The photograph is a close-up of the affected area. Female contributor, age 50–59. Reported lesion symptoms include itching. Reported duration is less than one week. Lay reviewers estimated Monk Skin Tone 1 or 2 (two reviewer pools). The affected area is the back of the torso: 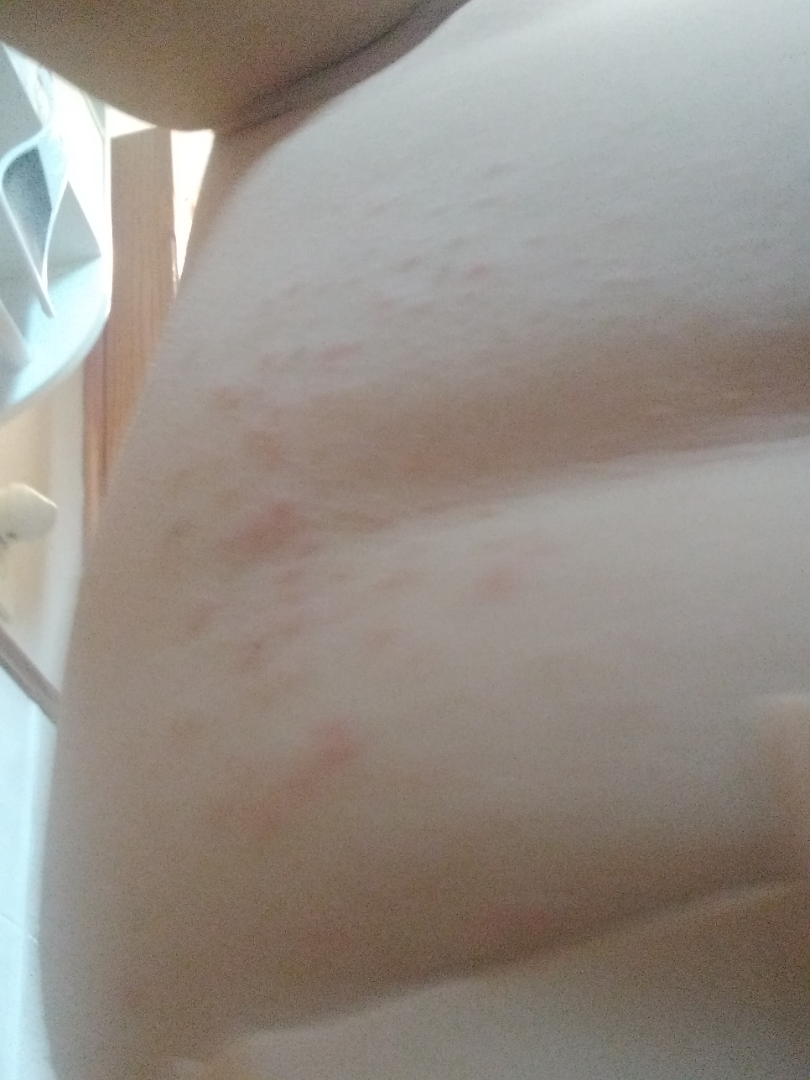Diagnostic features were not clearly distinguishable in this photograph.